The photograph is a close-up of the affected area. The patient notes the lesion is raised or bumpy. Symptoms reported: itching. The contributor is 30–39, female. The affected area is the front of the torso. The patient described the issue as a rash. The patient notes the condition has been present for about one day.
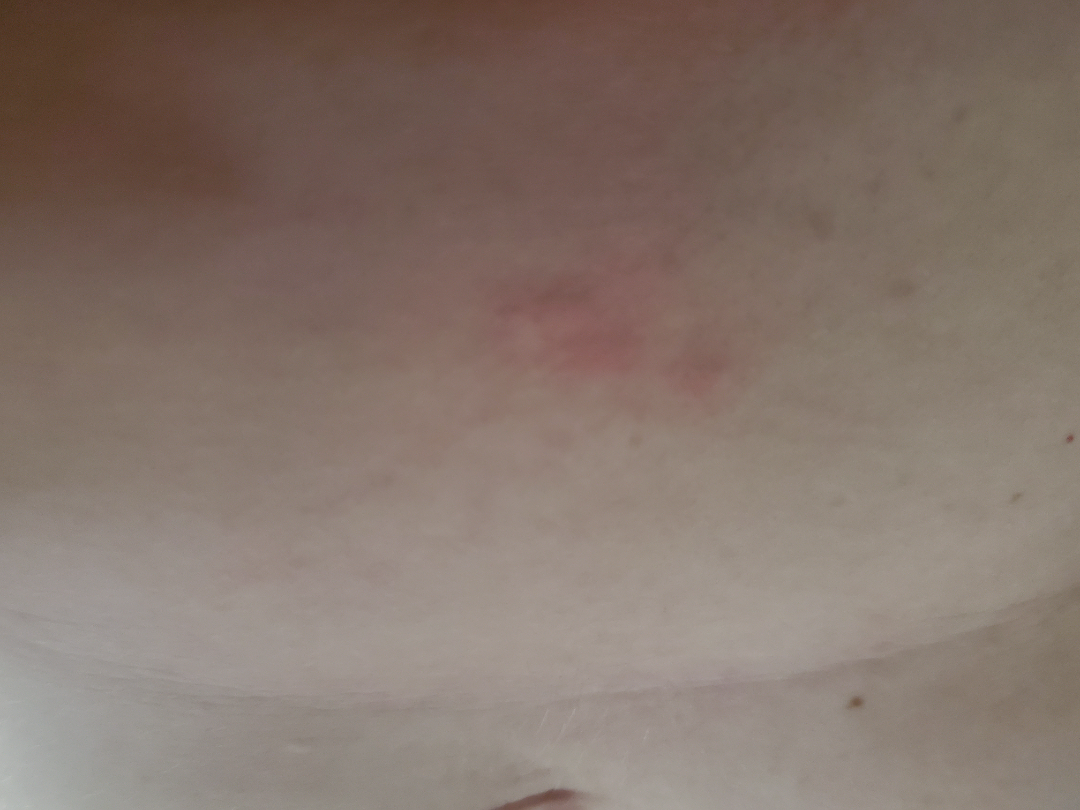The skin condition could not be confidently assessed from this image.